A dermoscopic photograph of a skin lesion: 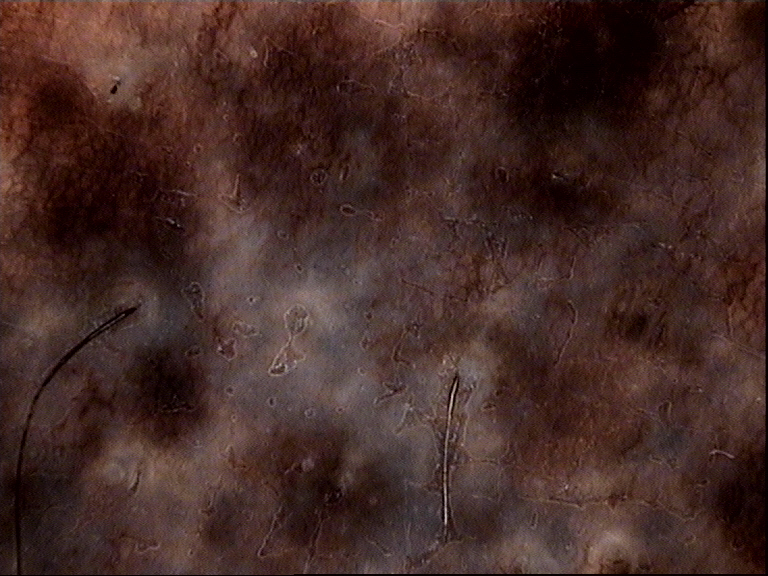The morphology is that of a banal lesion. The diagnosis was a congenital compound nevus.